Dermoscopy of a skin lesion.
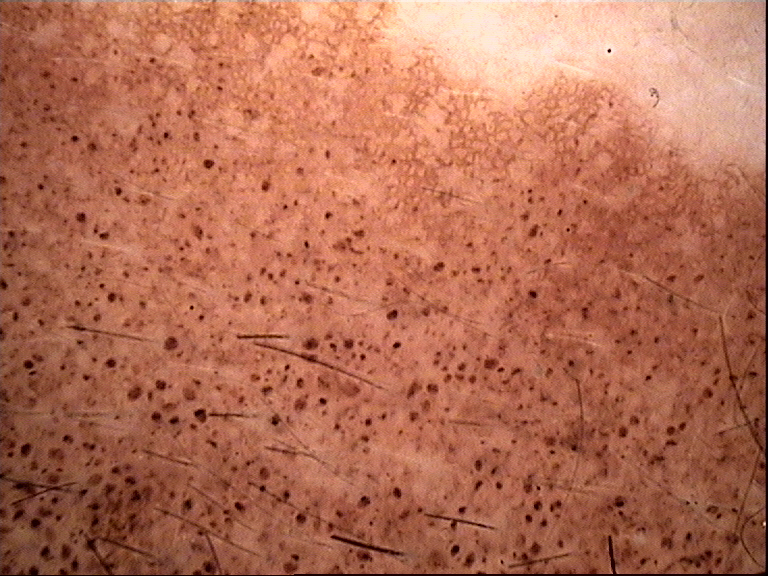<lesion>
<lesion_type>
<main_class>banal</main_class>
<pattern>junctional</pattern>
</lesion_type>
<diagnosis>
<name>congenital junctional nevus</name>
<code>cjb</code>
<malignancy>benign</malignancy>
<super_class>melanocytic</super_class>
<confirmation>expert consensus</confirmation>
</diagnosis>
</lesion>